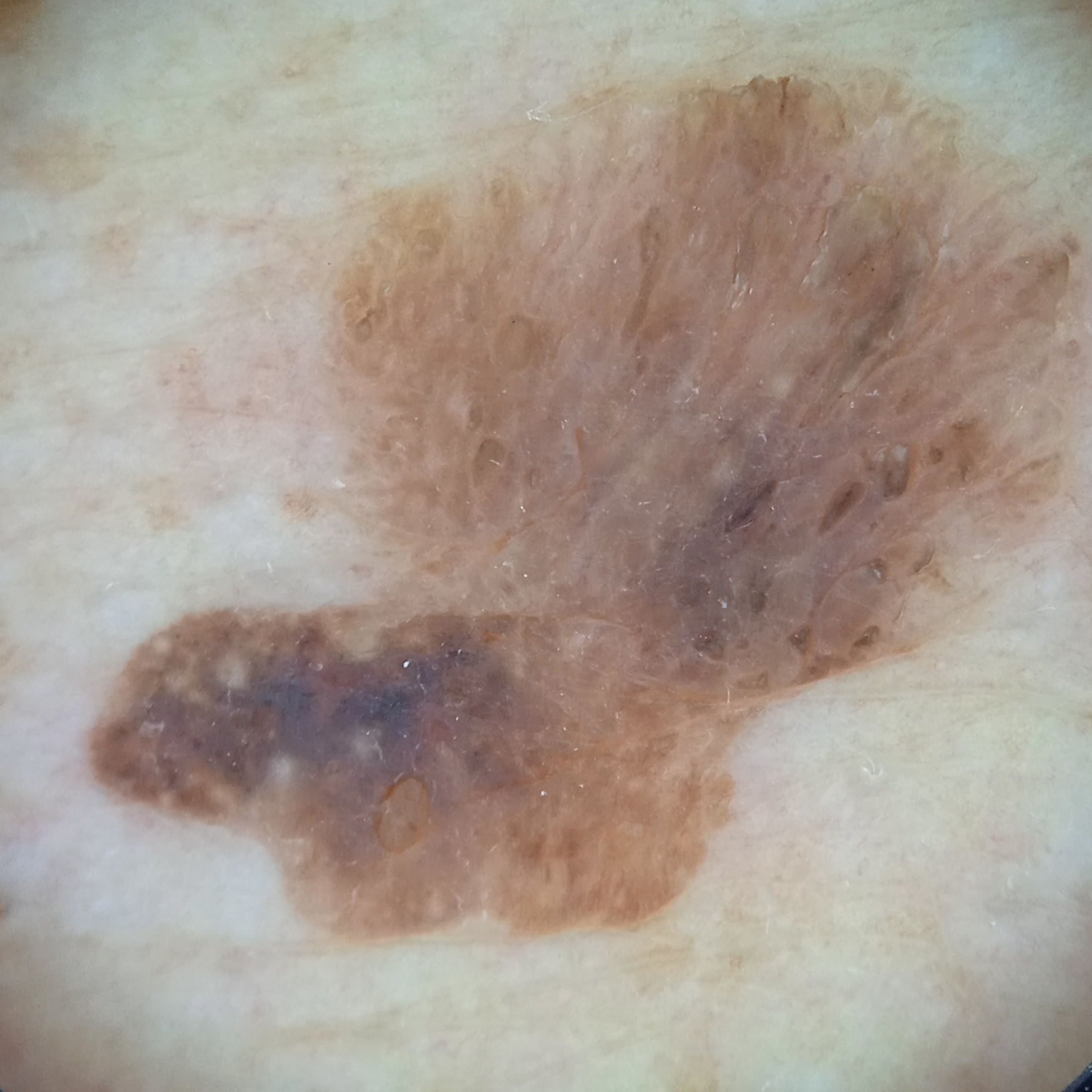Acquired for a research image collection, with no referral diagnosis. The patient says their skin tans without first burning. A male patient aged 72. A skin lesion imaged with a dermatoscope. The lesion involves the back. The dermatologists' assessment was a seborrheic keratosis.